A close-up photograph. The affected area is the front of the torso: 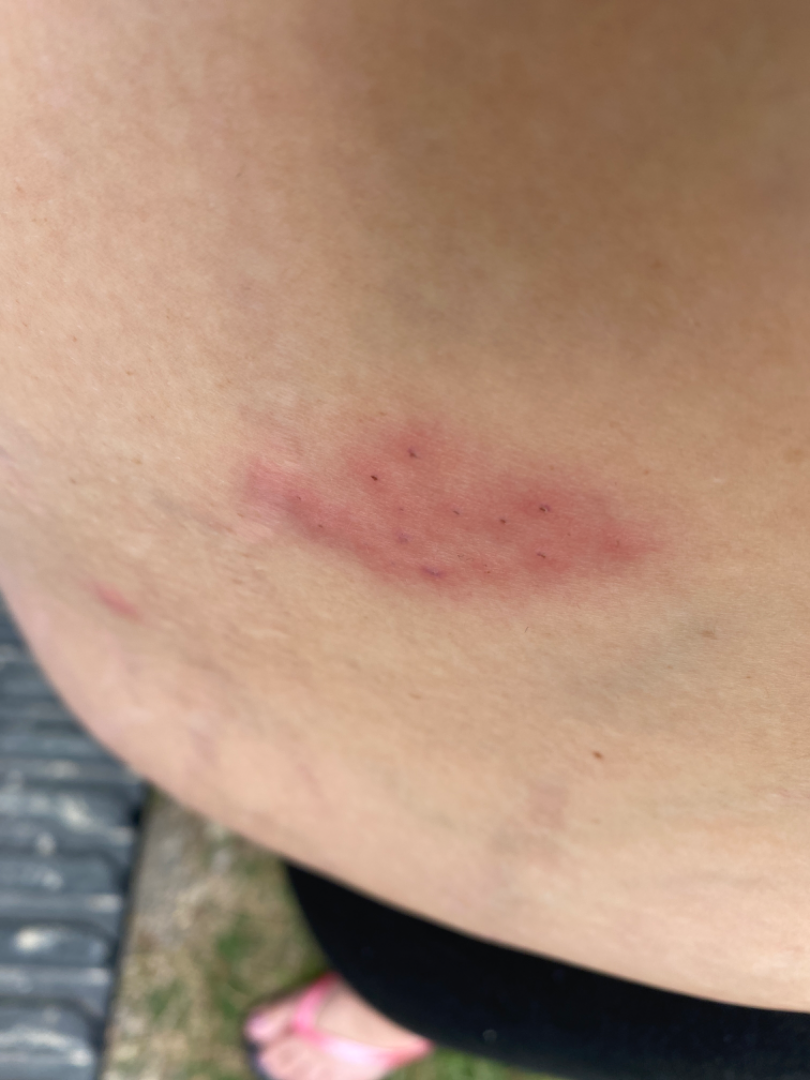On teledermatology review, most consistent with Herpes Zoster; the differential also includes Herpes Simplex; a remote consideration is Allergic Contact Dermatitis.